A female subject, aged around 60; a dermoscopic image of a skin lesion: 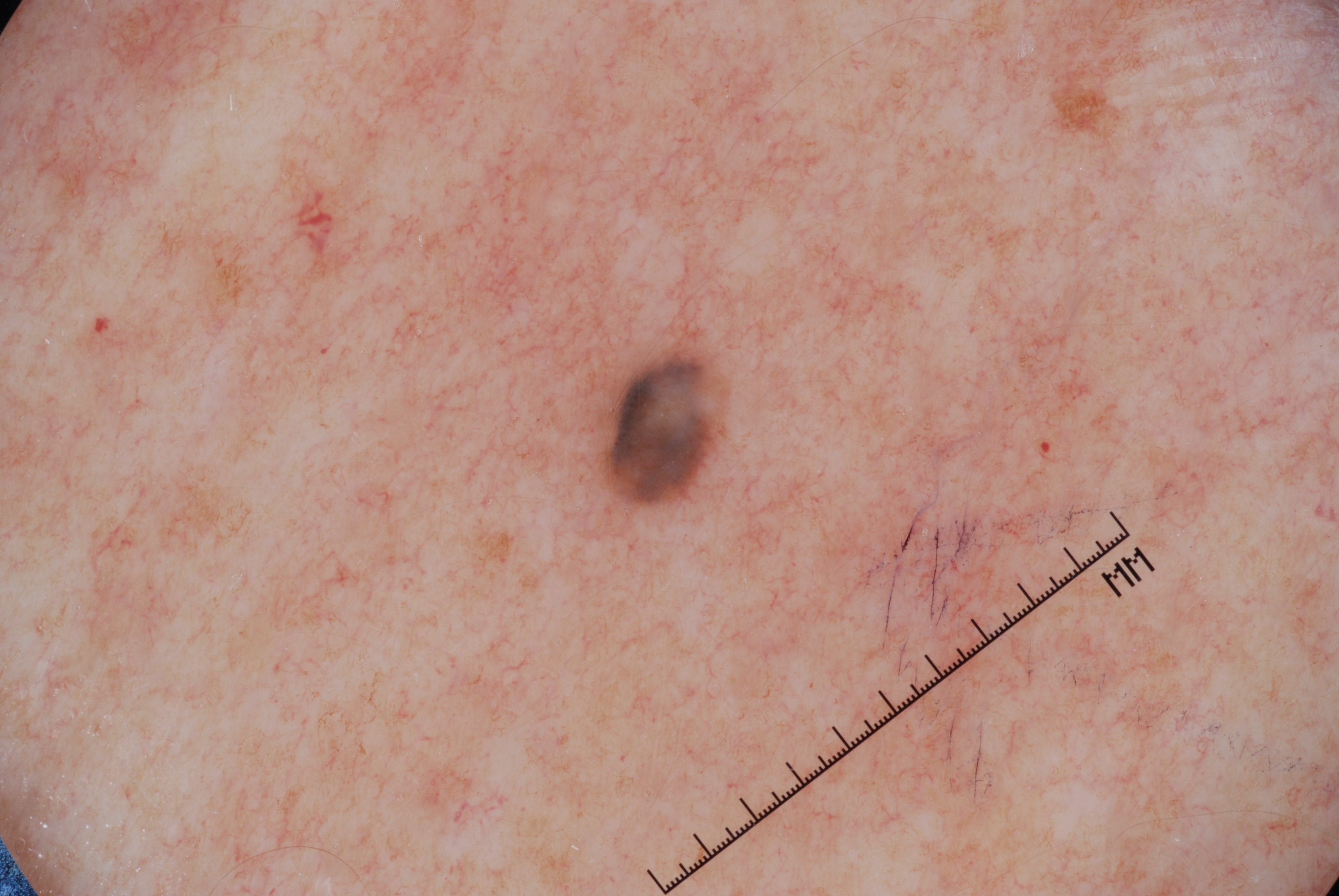The dermoscopic pattern shows no milia-like cysts, streaks, pigment network, or negative network. As (left, top, right, bottom), the lesion's extent is [565, 343, 732, 518]. Consistent with a melanocytic nevus, a benign skin lesion.